A female patient about 50 years old · dermoscopy of a skin lesion:
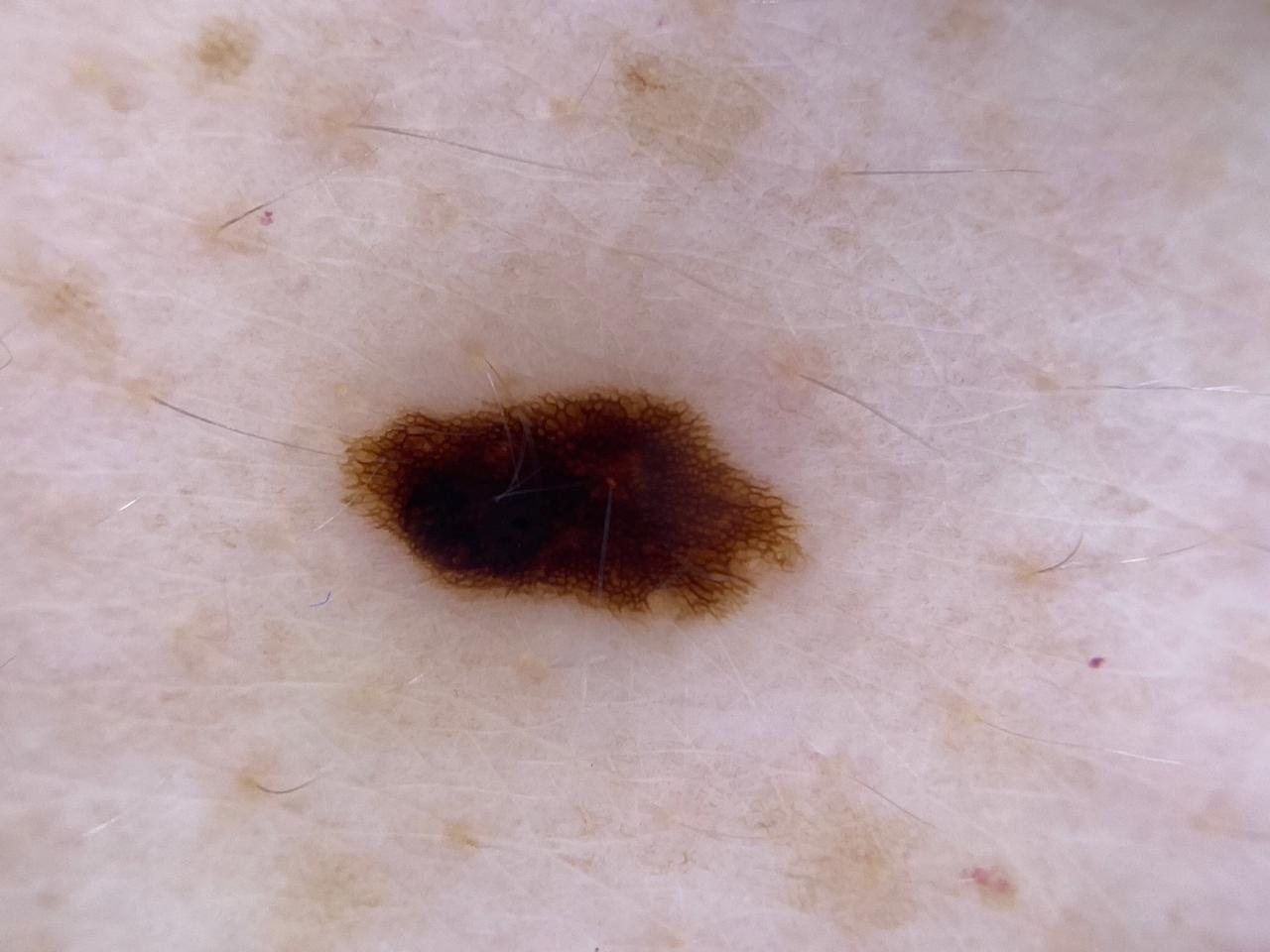{"lesion_location": {"region": "the trunk", "detail": "the anterior trunk"}, "diagnosis": {"name": "Nevus", "malignancy": "benign", "confirmation": "histopathology", "lineage": "melanocytic"}}